The affected area is the arm · a close-up photograph · no relevant systemic symptoms · the contributor notes the condition has been present for less than one week · the contributor notes the lesion is raised or bumpy · the lesion is associated with bothersome appearance and itching · self-categorized by the patient as a rash:
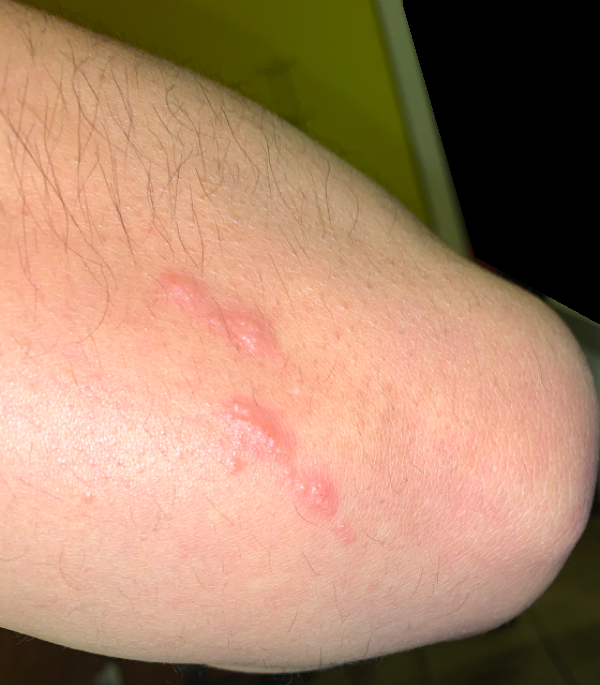Impression:
The case was indeterminate on photographic review.